This is a close-up image — 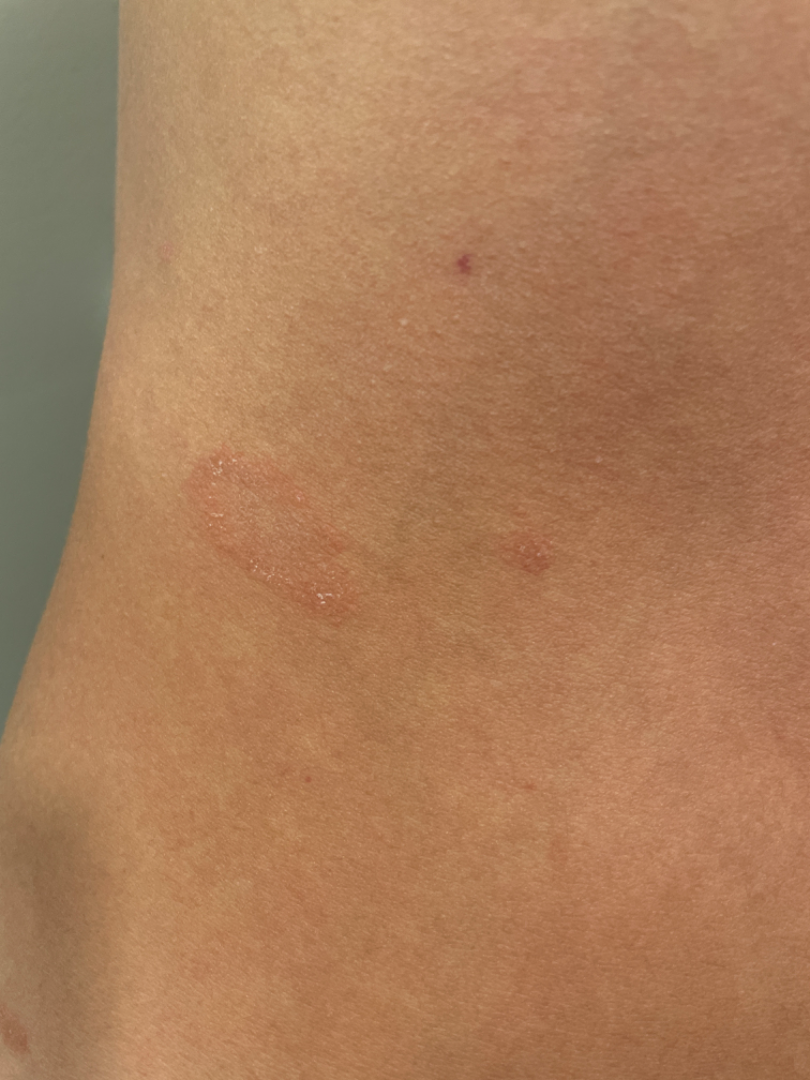Most likely Pityriasis rosea.